A male subject aged 78-82. FST II. A dermoscopic close-up of a skin lesion. Per the chart, a prior melanoma.
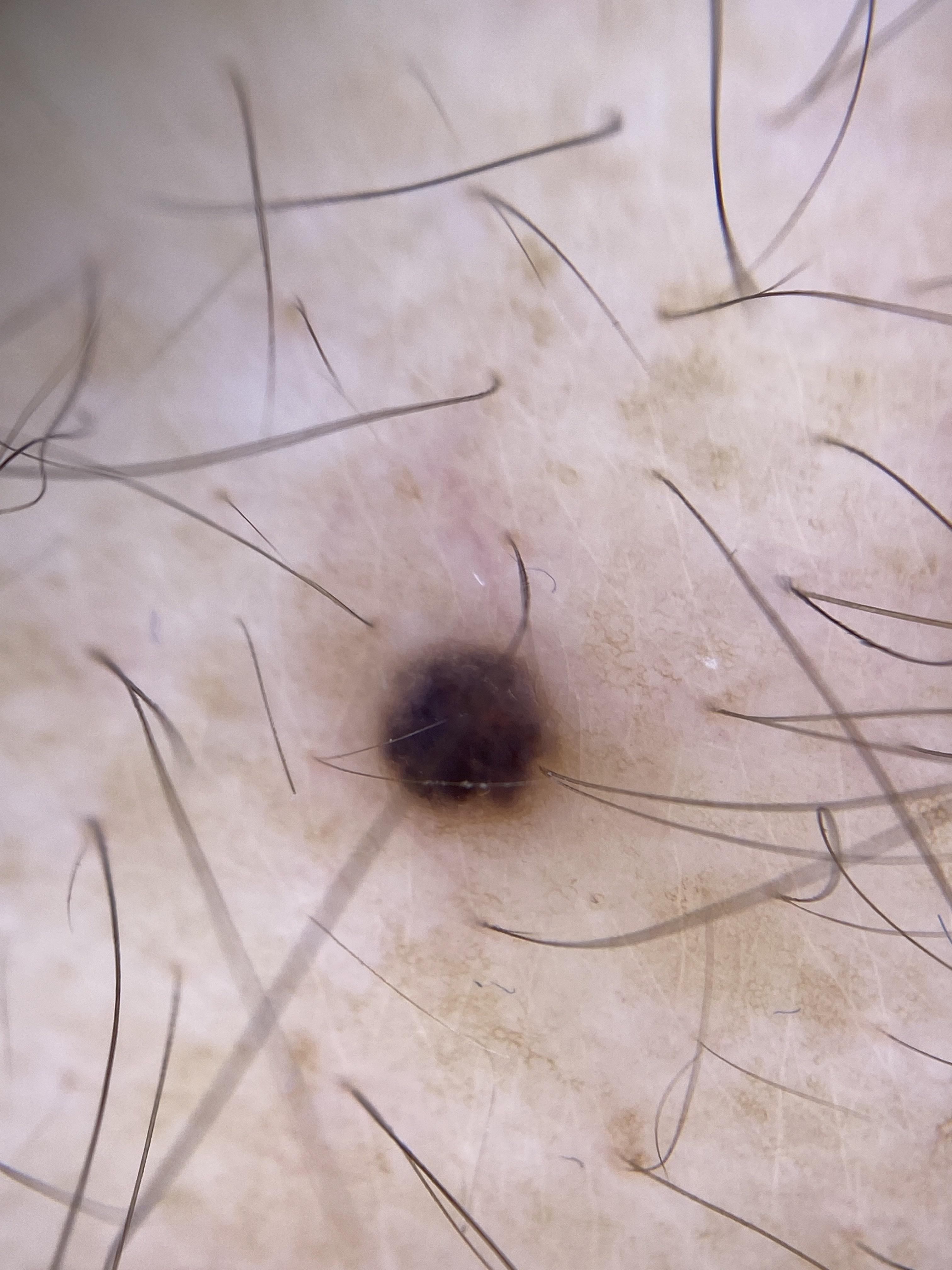The lesion was found on the trunk. Histopathologically confirmed as a melanocytic lesion — a nevus.